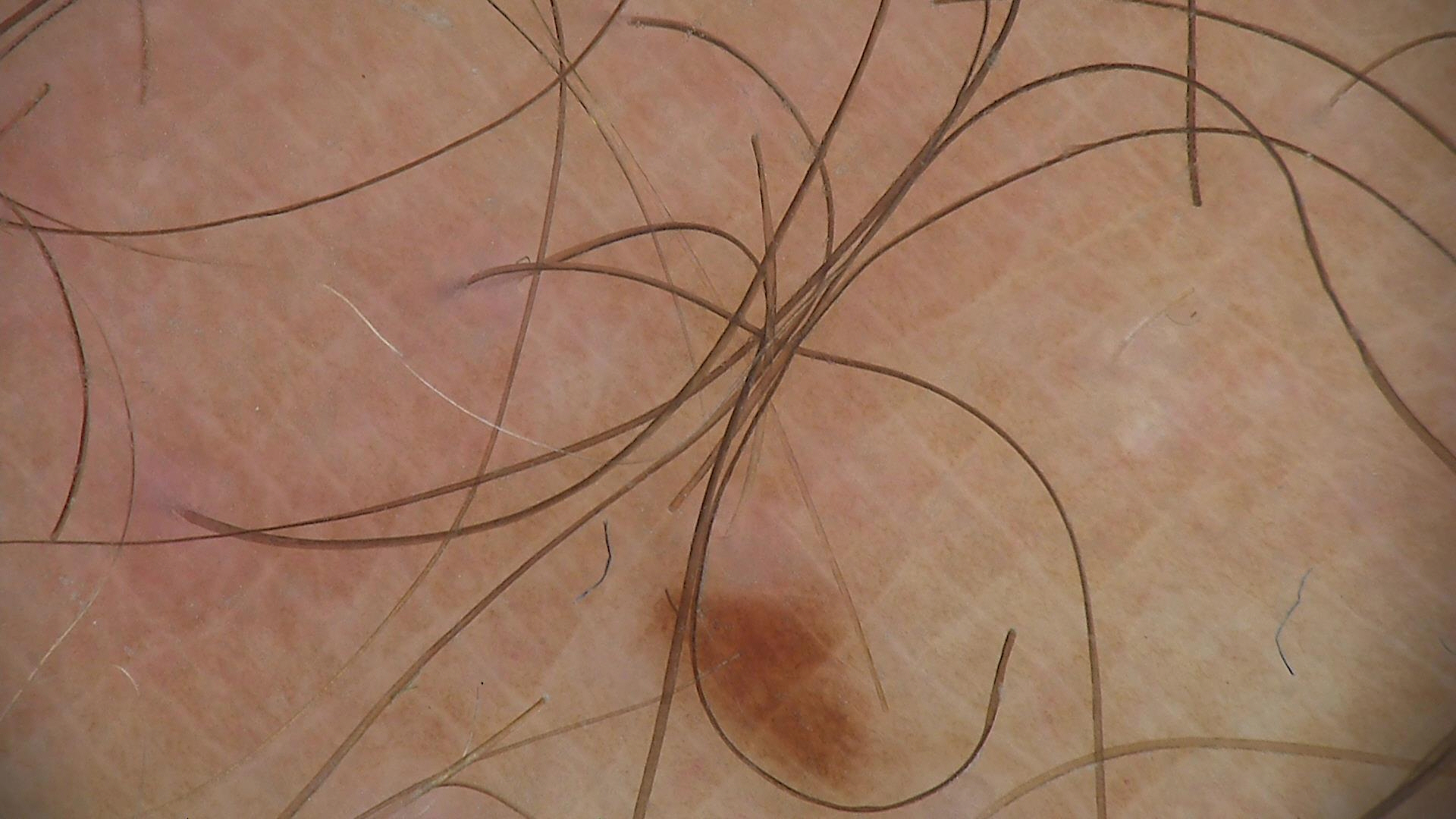subtype: banal, class: junctional nevus (expert consensus).